A dermoscopic close-up of a skin lesion: 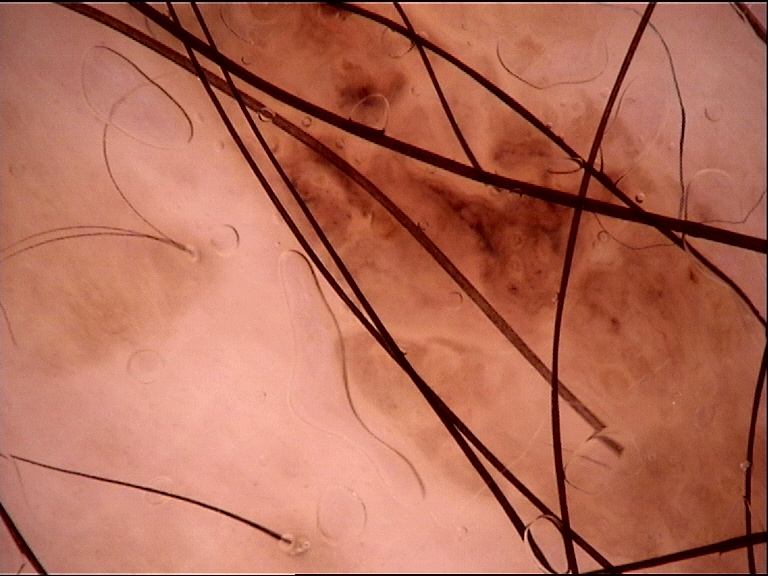Diagnosed as a banal lesion — a compound nevus.